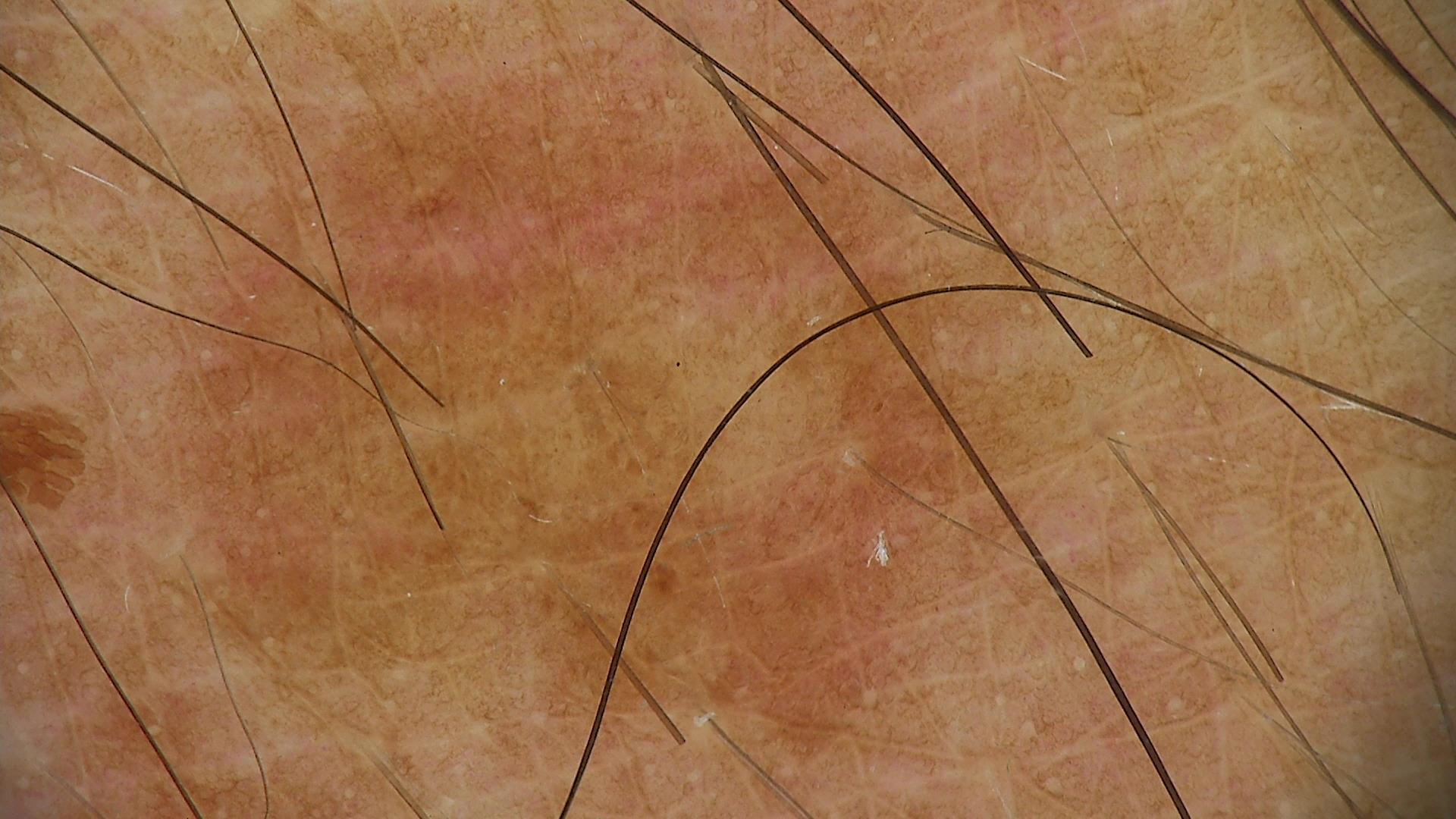Consistent with a dysplastic junctional nevus.